This image was taken at a distance — 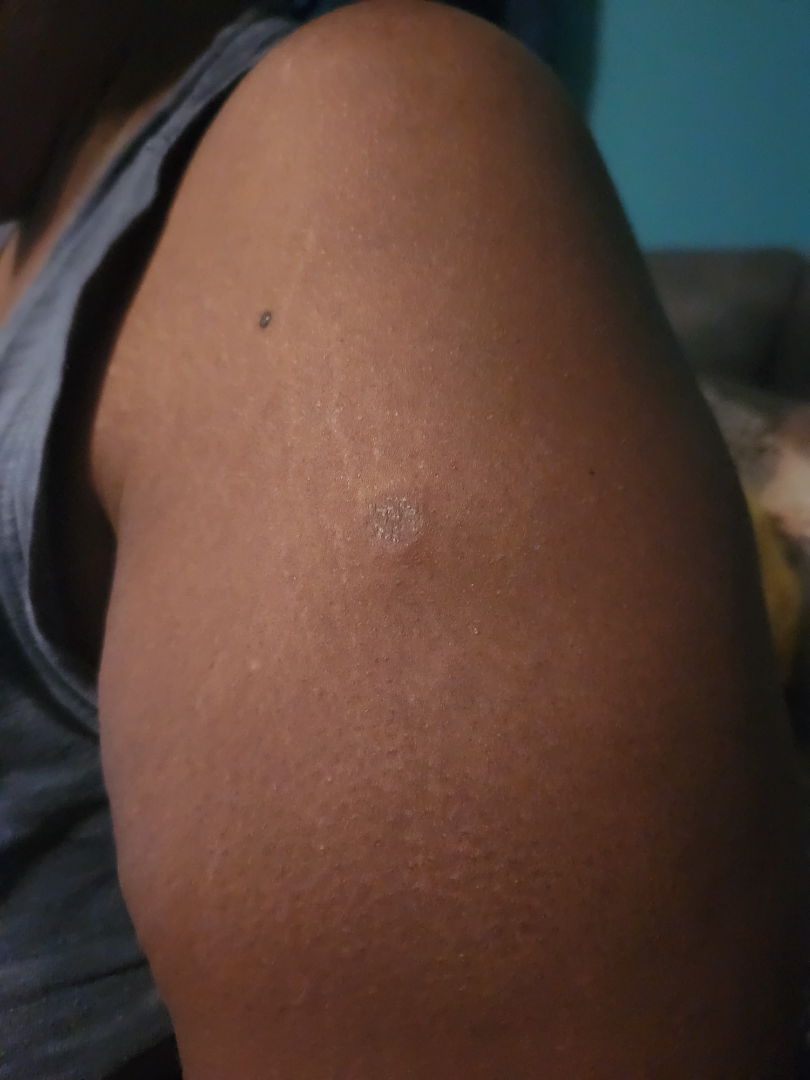Q: What conditions are considered?
A: Fungal dermatosis and SCC/SCCIS were each considered, in no particular order; less probable is Tuberculosis of skin and subcutaneous tissue